The chart records a prior melanoma but no melanoma in first-degree relatives · a female subject aged 73-77 · FST II · a contact-polarized dermoscopy image of a skin lesion — 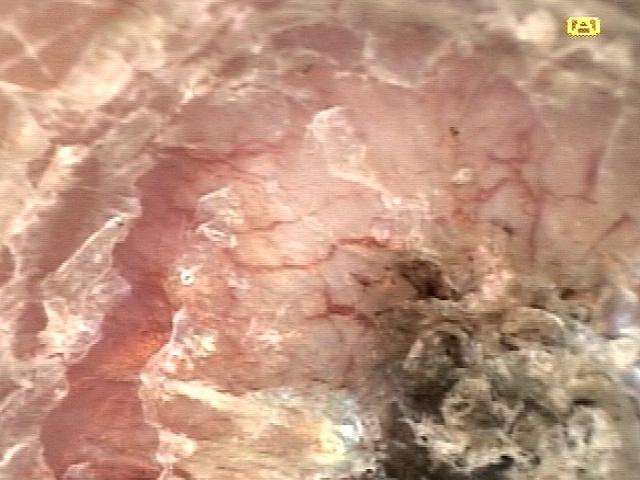anatomic site — a lower extremity
diagnostic label — Squamous cell carcinoma (biopsy-proven)